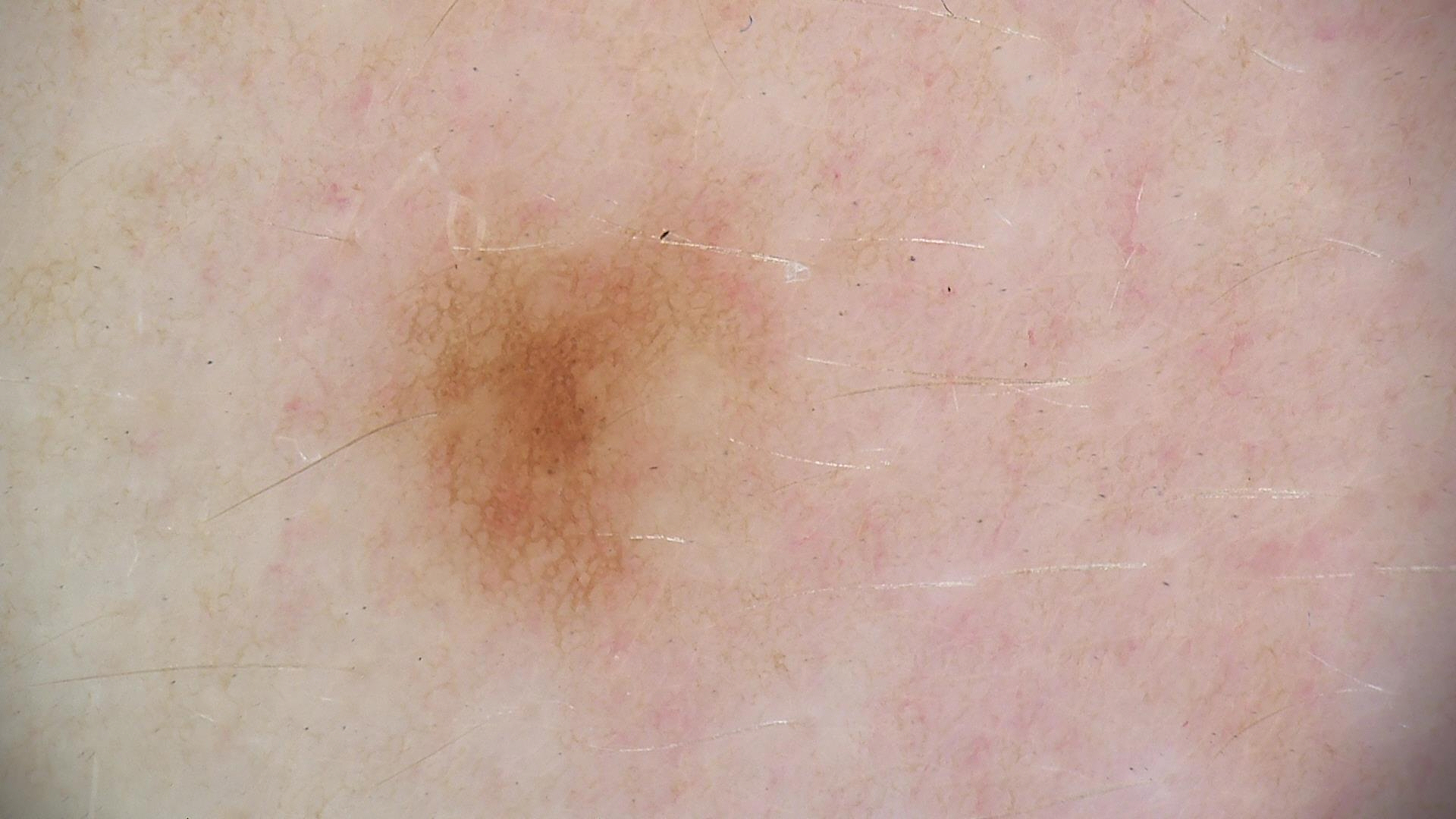Consistent with a dysplastic junctional nevus.